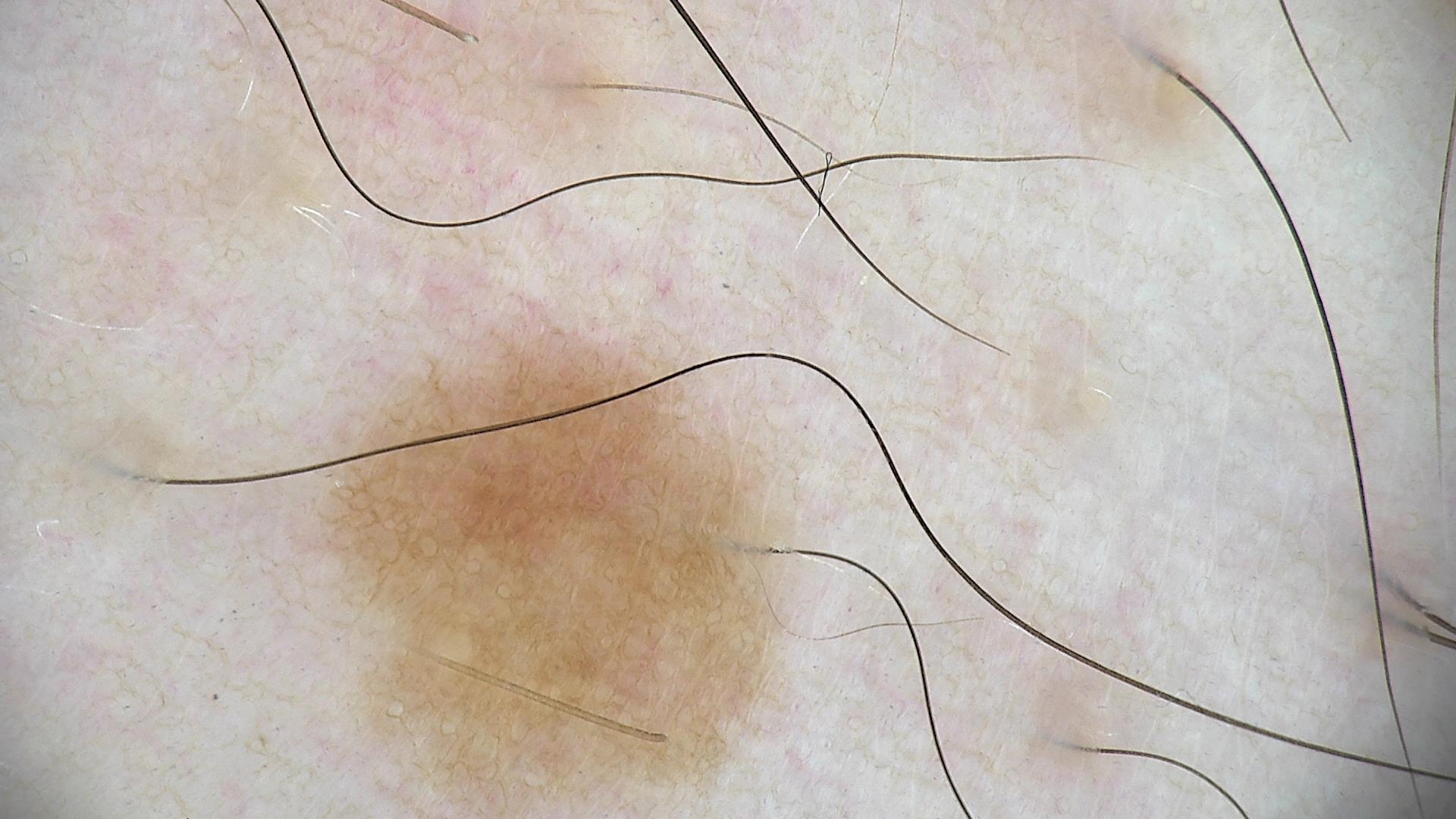Consistent with a dysplastic junctional nevus.